The lesion is described as raised or bumpy and fluid-filled · the condition has been present for about one day · self-categorized by the patient as a rash · the patient also reports fever, fatigue and chills · symptoms reported: bothersome appearance, itching and pain · located on the back of the torso and front of the torso · the photo was captured at a distance.
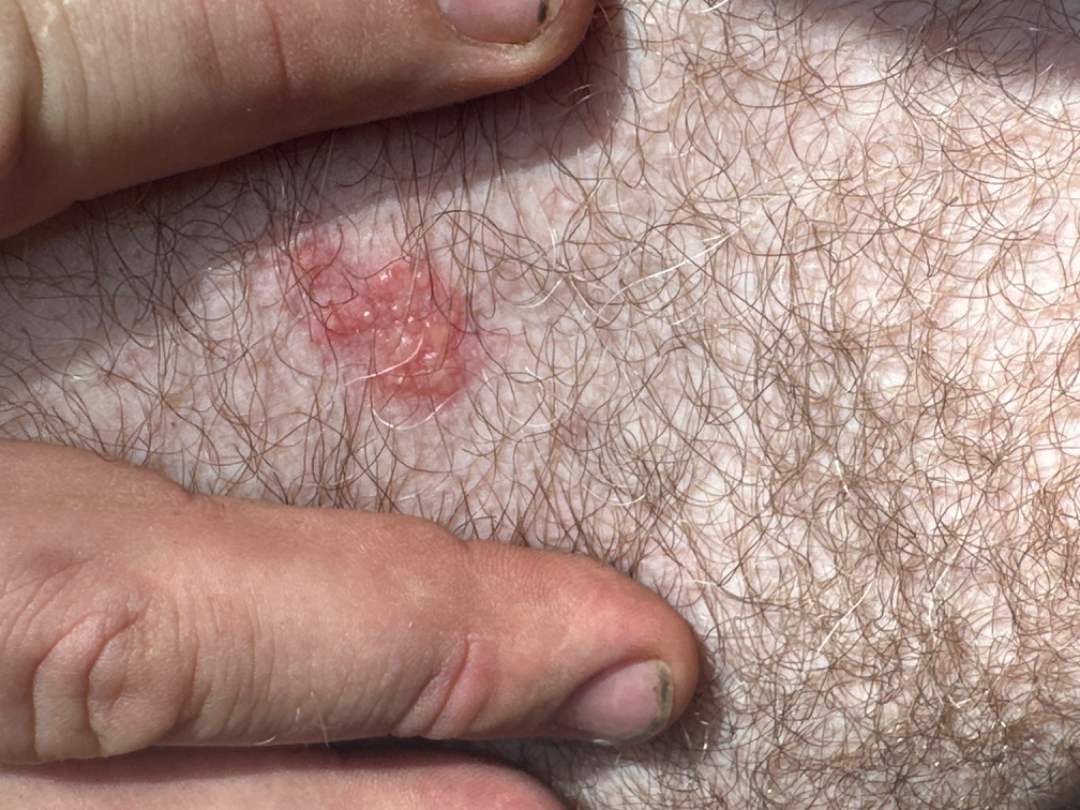Most likely Condyloma acuminatum; possibly Melanocytic Nevus.